This is a dermoscopic photograph of a skin lesion.
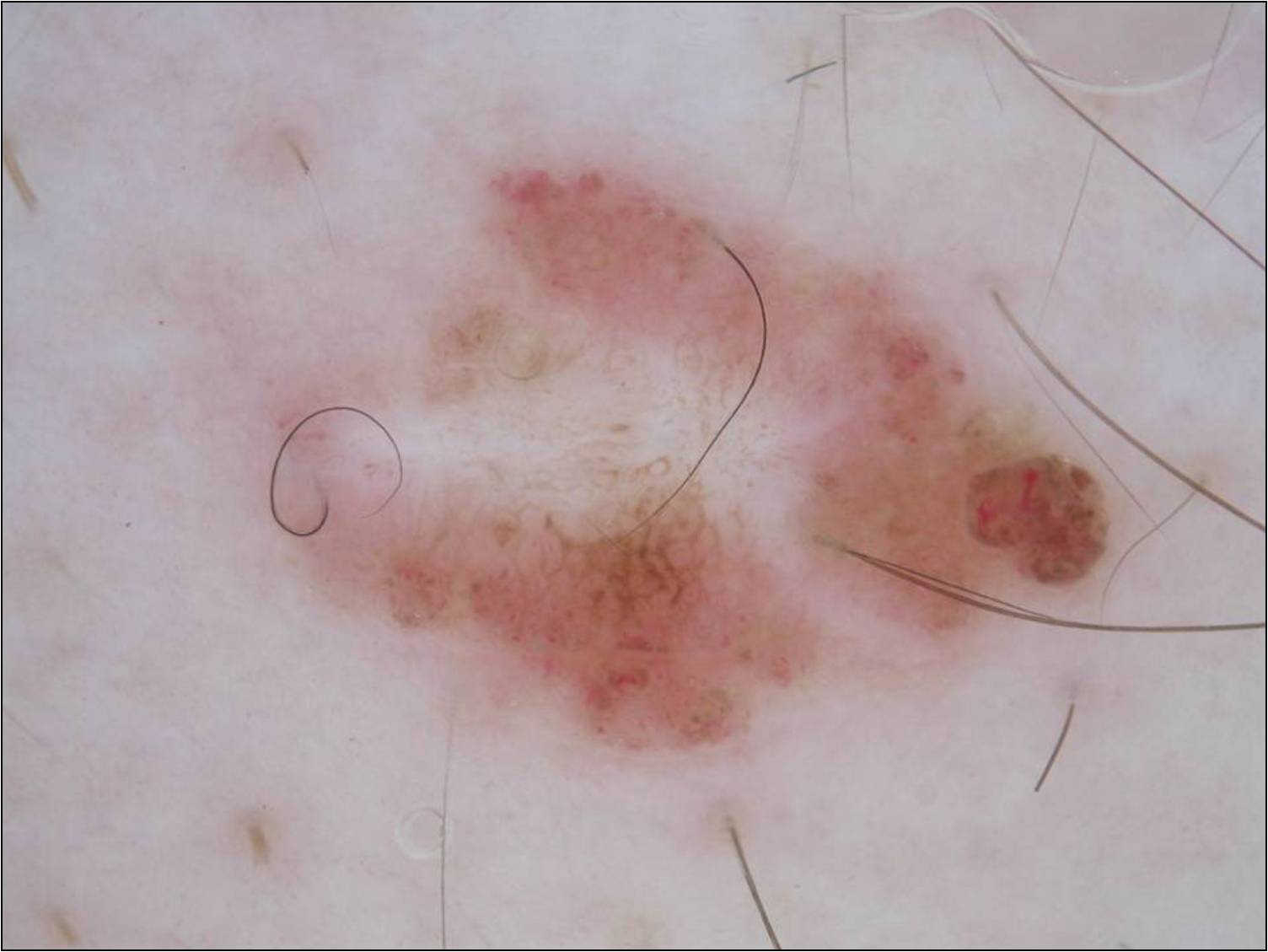Notes:
• features — pigment network and globules
• bounding box — [256, 165, 1115, 774]
• lesion size — moderate
• assessment — a melanocytic nevus, a benign lesion